Contact-polarized dermoscopy of a skin lesion. The chart notes no prior melanoma and no melanoma in first-degree relatives.
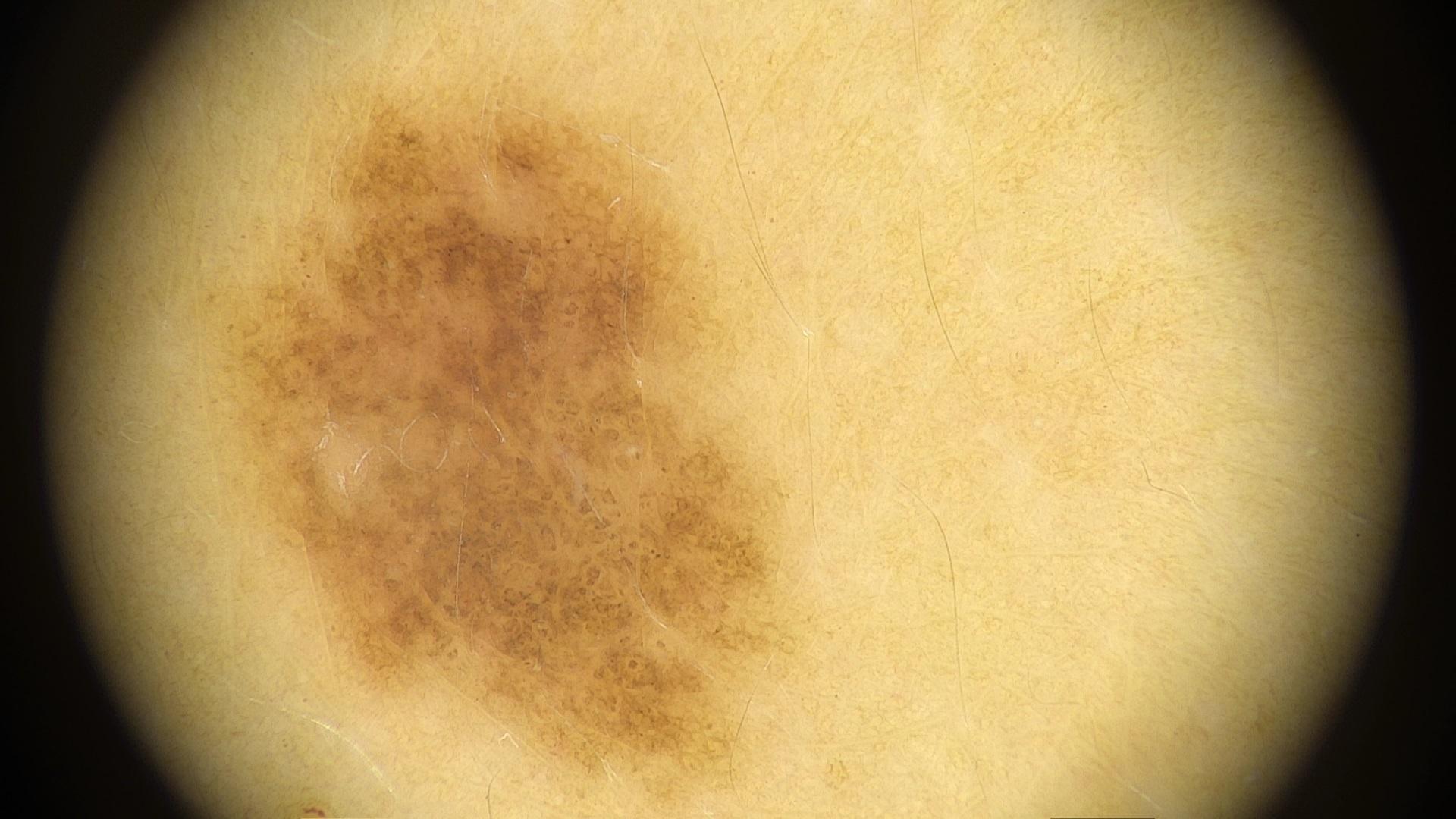The lesion was found on the trunk.
The clinical assessment was a nevus.